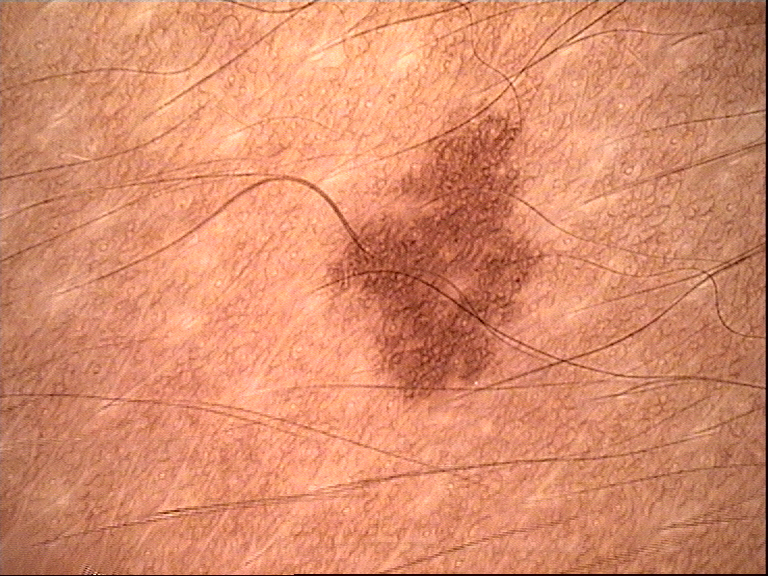- imaging — dermoscopy
- class — dysplastic junctional nevus (expert consensus)